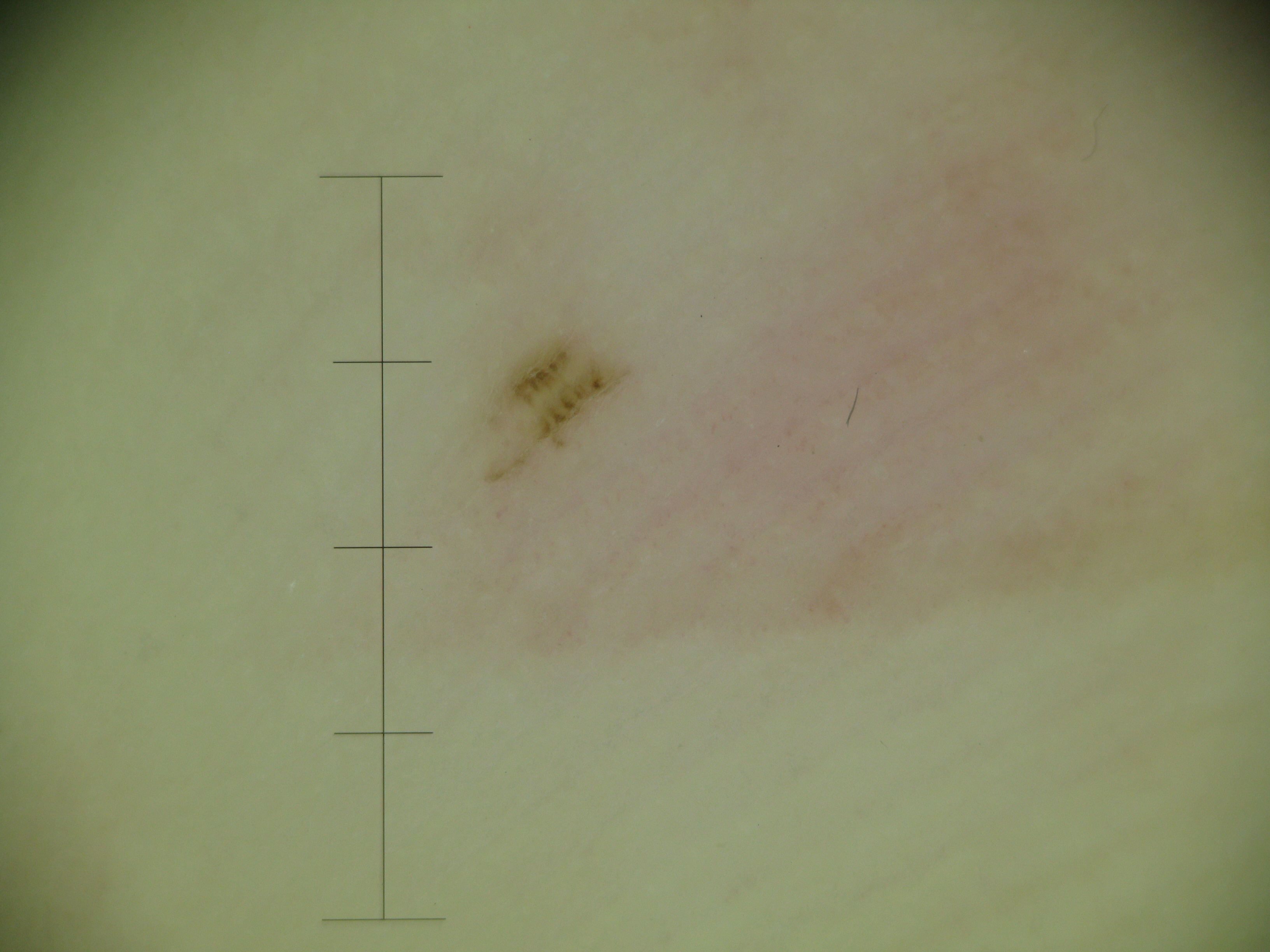| field | value |
|---|---|
| image | dermoscopy |
| diagnosis | acral junctional nevus (expert consensus) |